Self-categorized by the patient as a rash; the lesion is associated with itching; located on the leg and arm; this is a close-up image; the patient indicates the lesion is raised or bumpy; the patient indicates the condition has been present for one to three months; female subject, age 18–29; Fitzpatrick skin type III:
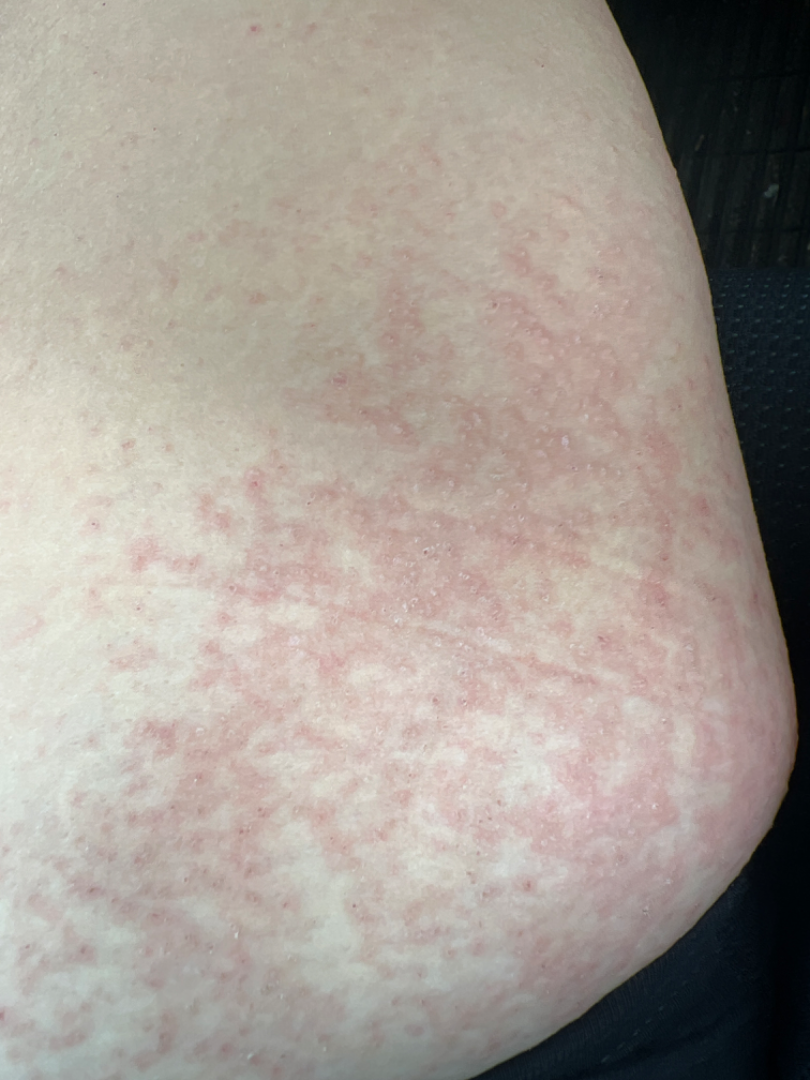{"differential": {"tied_lead": ["Miliaria", "Acute generalised exanthematous pustulosis"]}}